A clinical close-up photograph of a skin lesion:
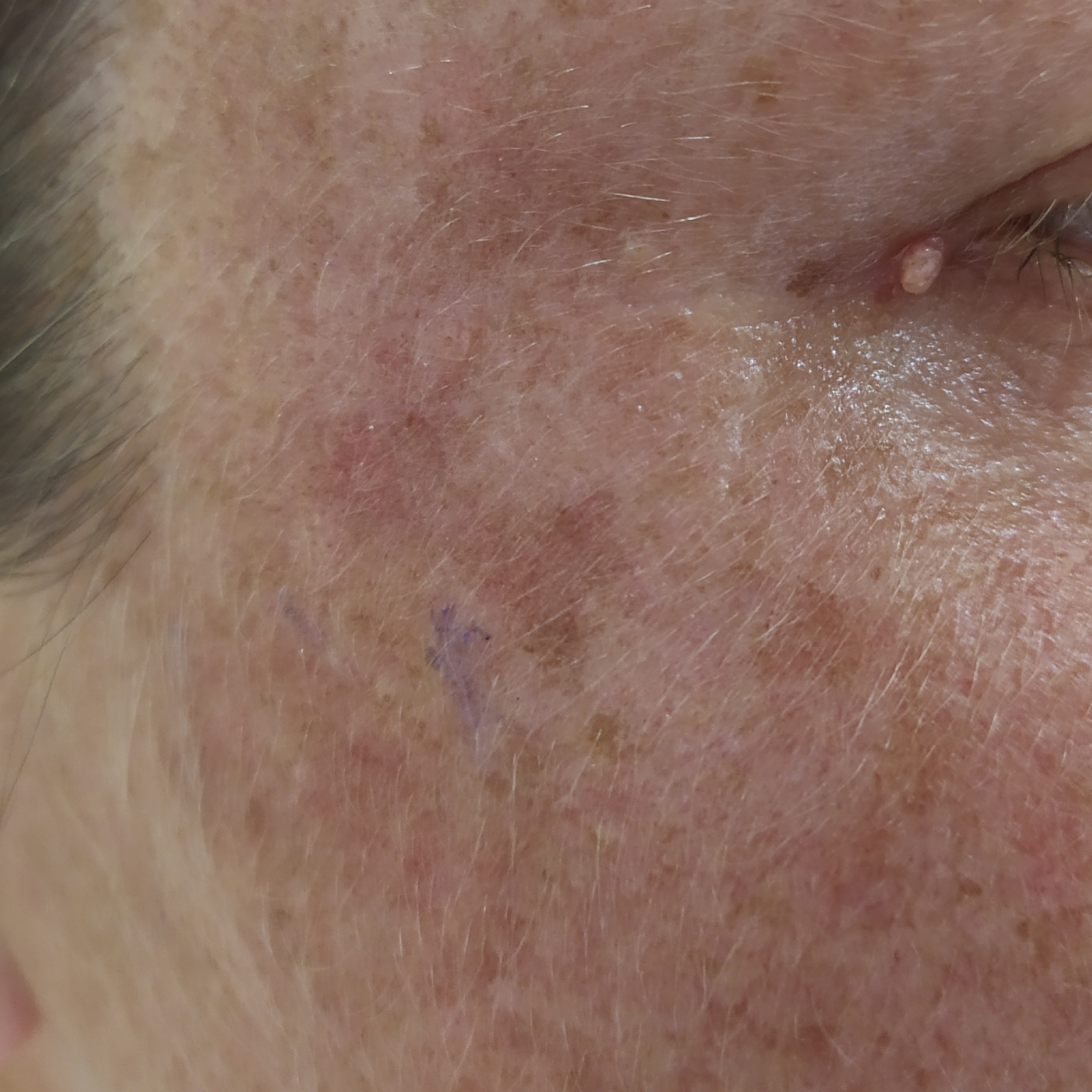Patient and lesion: The lesion was found on the face. Per patient report, the lesion itches and has grown, but has not changed. Conclusion: Expert review favored an actinic keratosis.